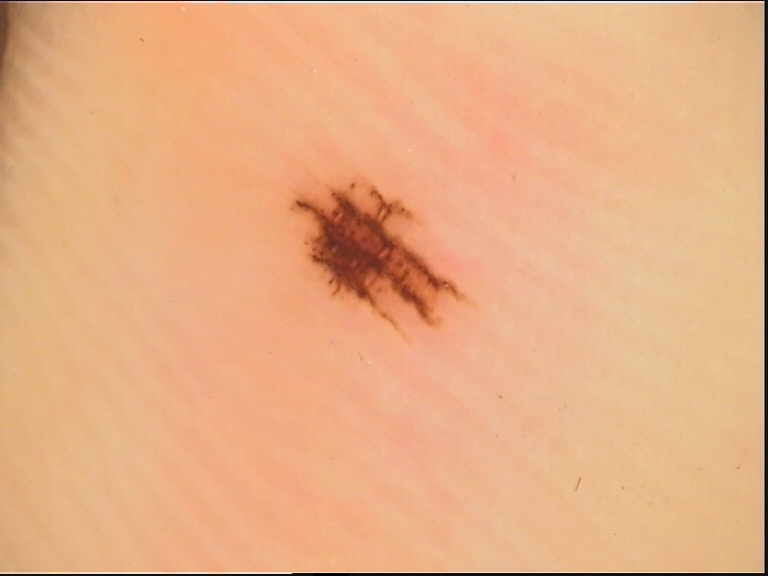A dermoscopic photograph of a skin lesion. Diagnosed as a benign lesion — an acral dysplastic junctional nevus.